This image was taken at a distance; the affected area is the head or neck, leg, arm, back of the hand and front of the torso — 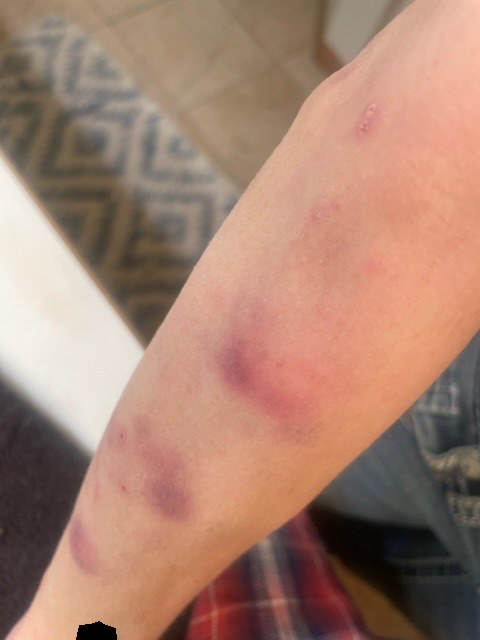The skin findings could not be characterized from the image.
The patient reports the lesion is flat and raised or bumpy.
Present for one to four weeks.
No relevant systemic symptoms.
The patient considered this skin that appeared healthy to them.